Located on the leg; the patient considered this a rash; the lesion is described as flat; the patient reported no systemic symptoms; female contributor, age 60–69; the photo was captured at a distance; reported duration is less than one week.
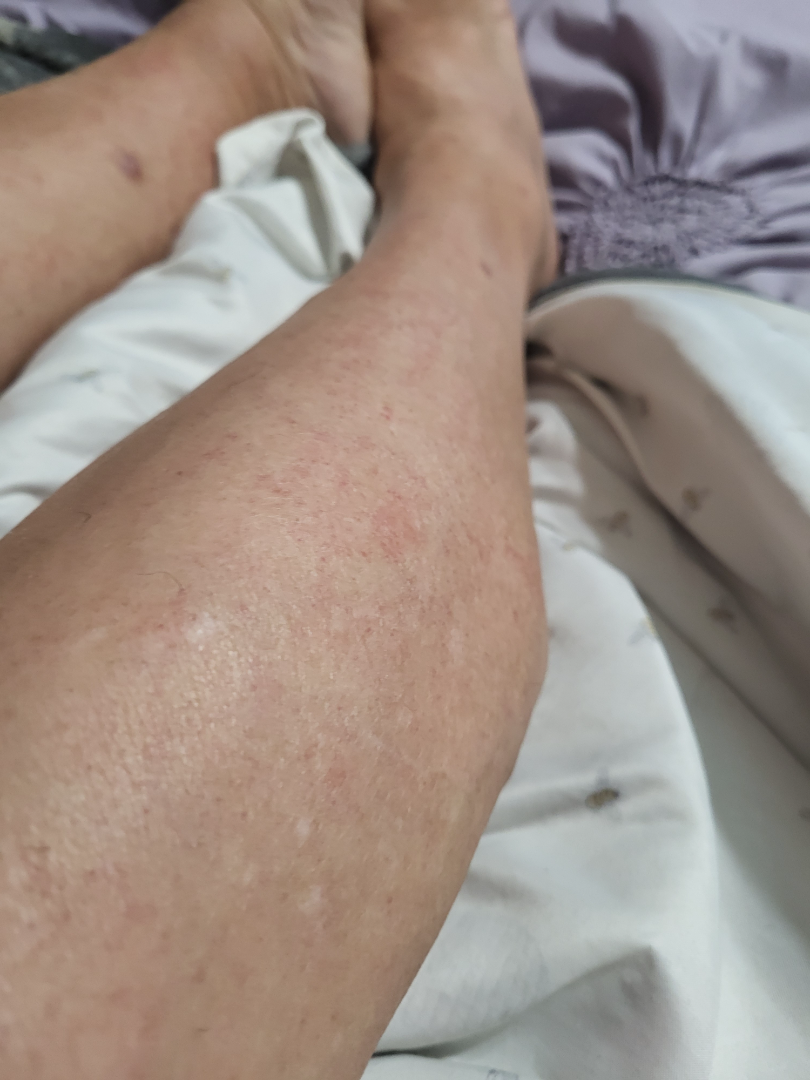Findings:
* dermatologist impression · Stasis Dermatitis (primary); Allergic Contact Dermatitis (possible); Pigmented purpuric eruption (possible)